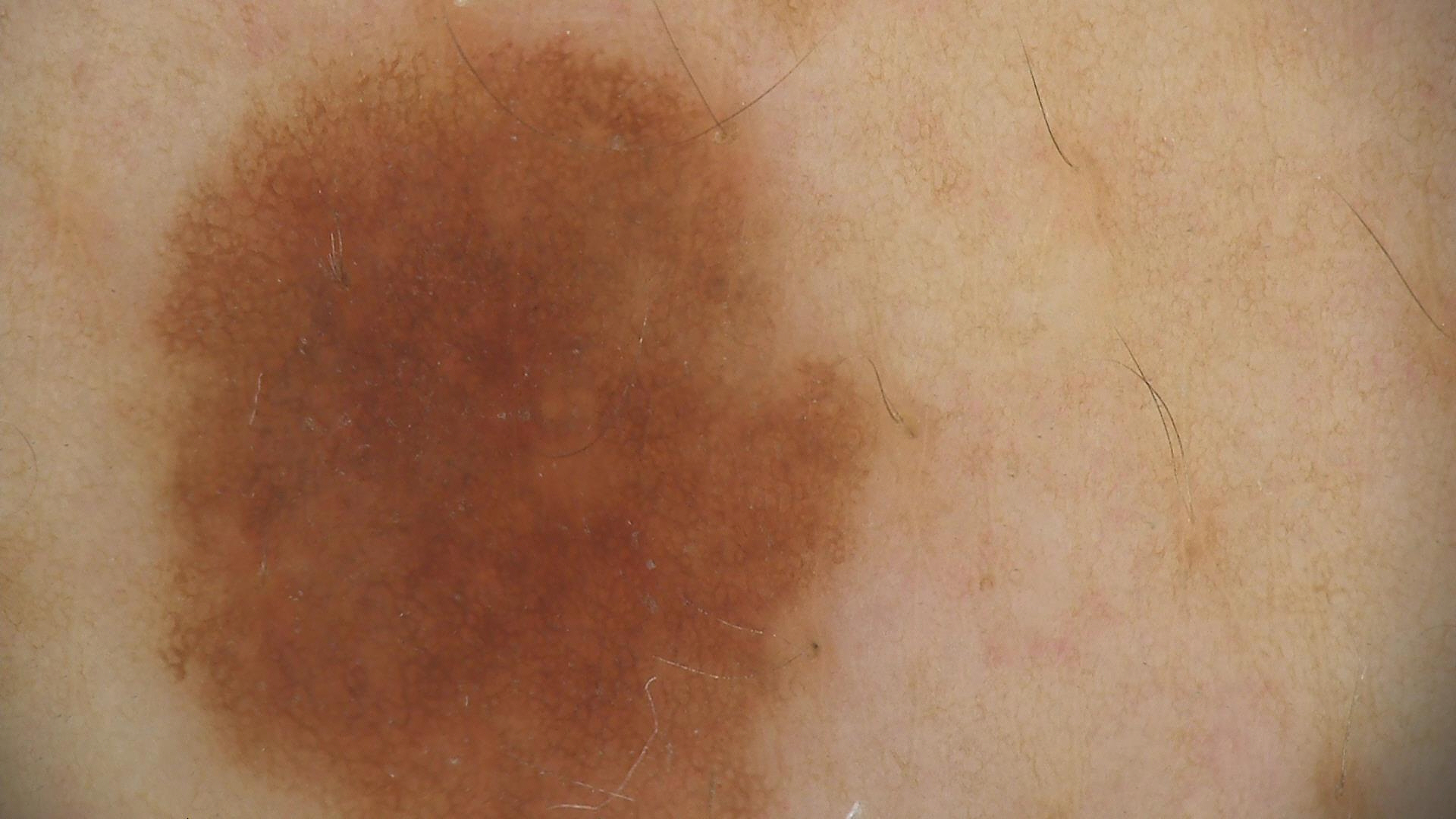| field | value |
|---|---|
| assessment | dysplastic junctional nevus (expert consensus) |